A dermatoscopic image of a skin lesion; collected as part of a research study, without a referral diagnosis; a female patient 78 years of age.
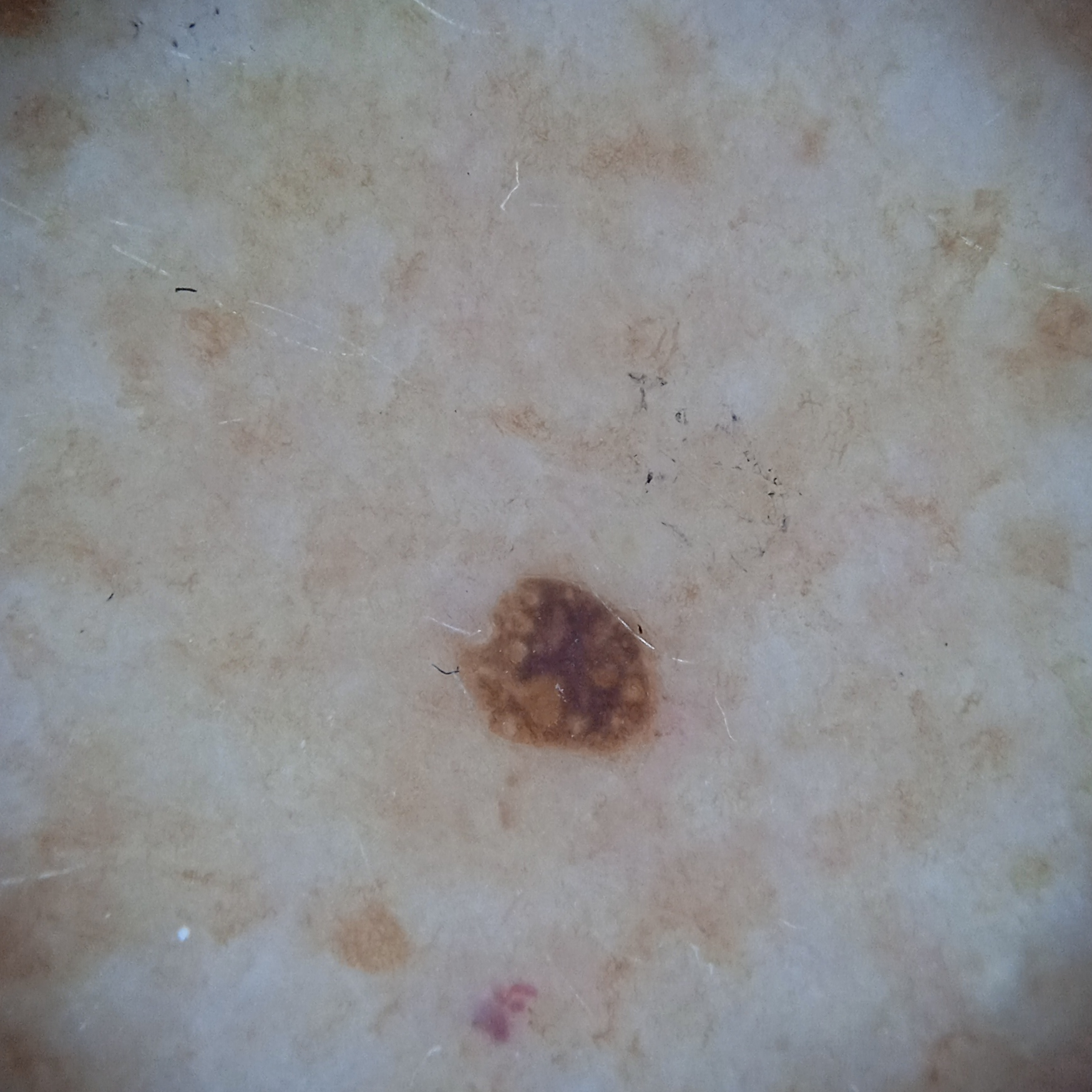Case summary:
The lesion involves an arm. Measuring roughly 2.4 mm.
Assessment:
Dermatologist review favored a seborrheic keratosis.